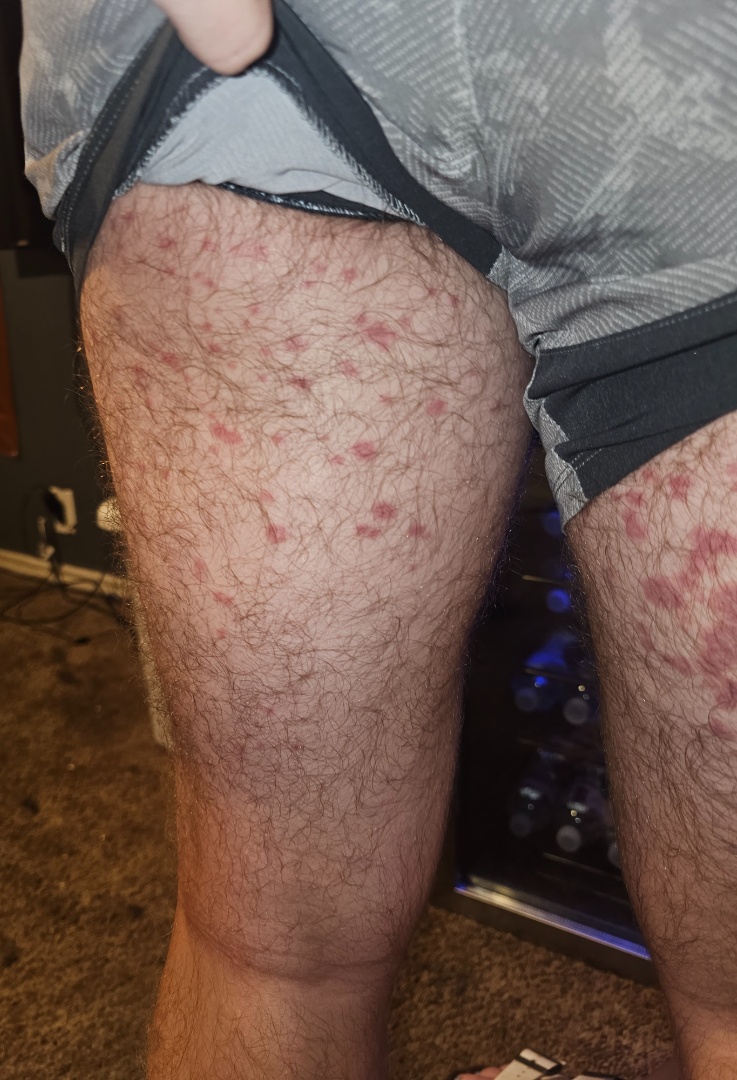duration: less than one week
shot_type: close-up
body_site: leg
differential:
  tied_lead:
    - Drug Rash
    - Leukocytoclastic Vasculitis